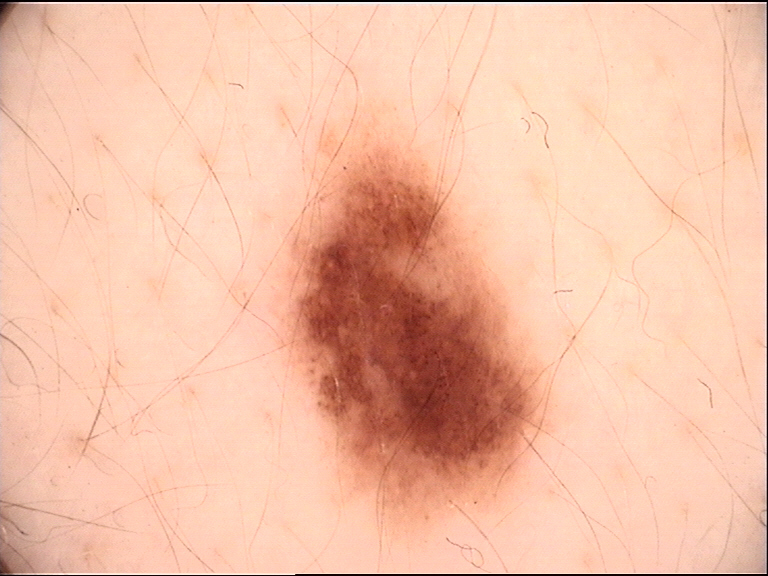diagnosis: dysplastic junctional nevus (expert consensus).